The photograph was taken at a distance.
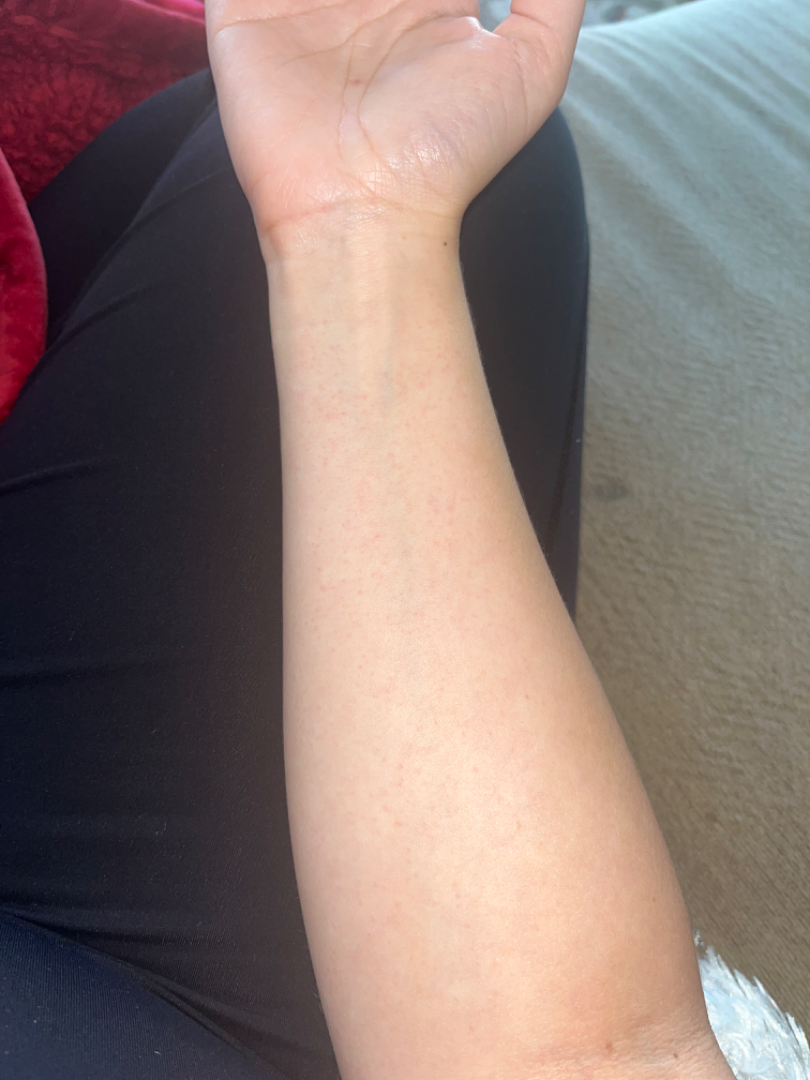Diagnostic features were not clearly distinguishable in this photograph.